A dermatoscopic image of a skin lesion.
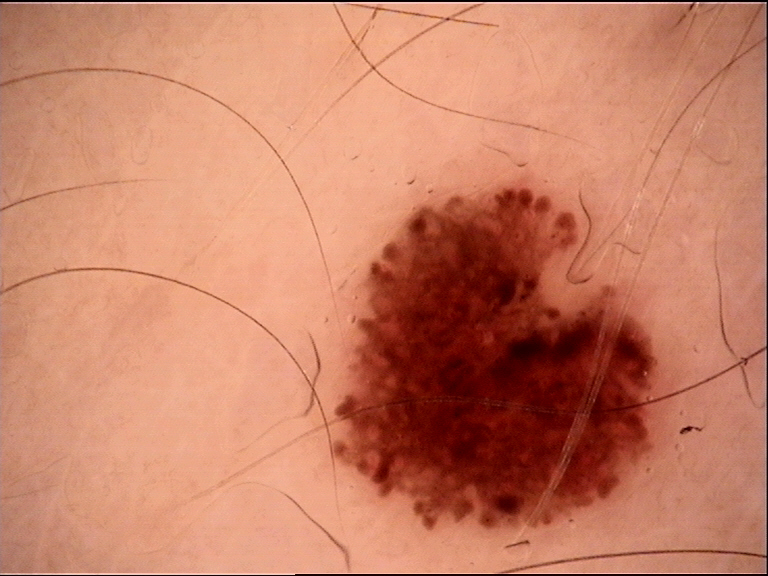- class: dysplastic junctional nevus (expert consensus)